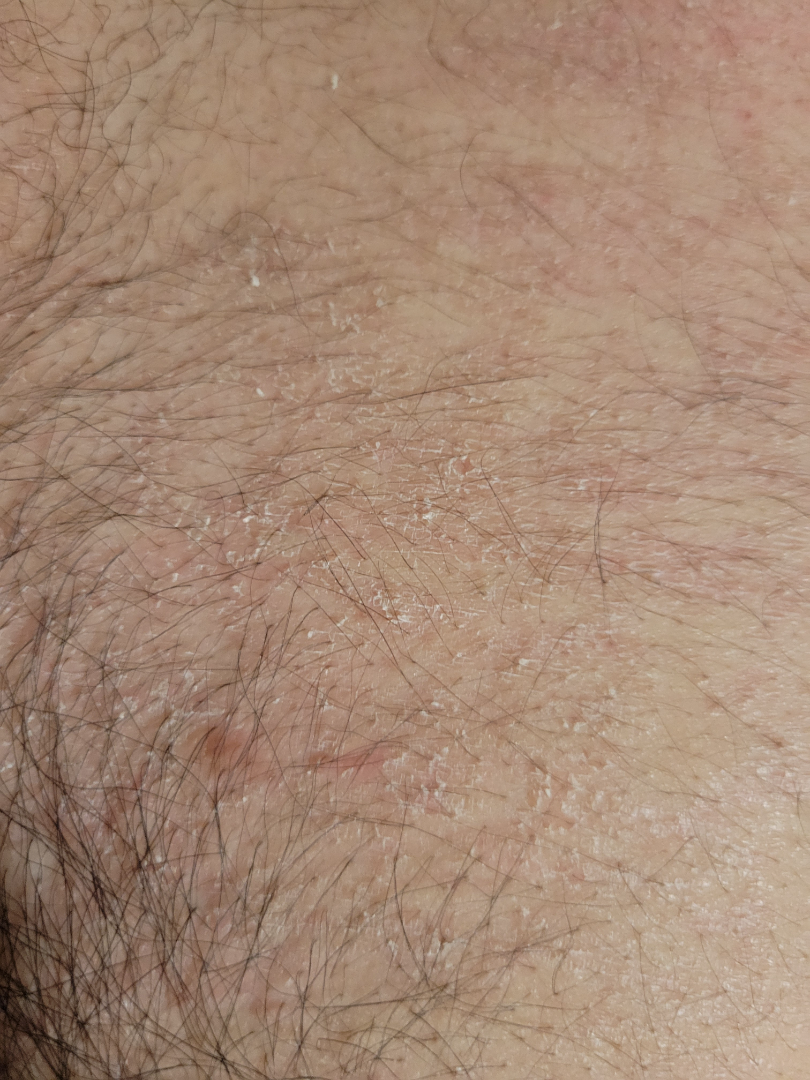assessment: Eczema (50%); Pityriasis lichenoides (25%); Tinea (25%)